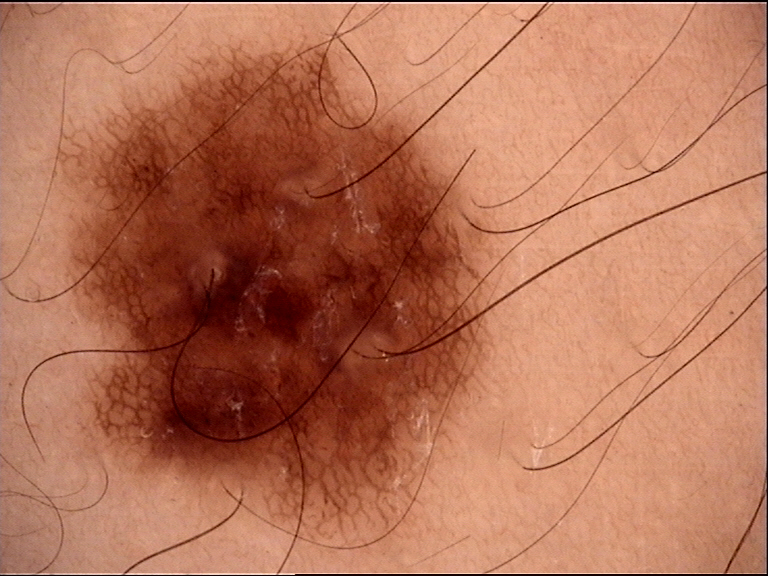<dermoscopy>
<image>dermoscopy</image>
<diagnosis>
<name>dysplastic junctional nevus</name>
<code>jd</code>
<malignancy>benign</malignancy>
<super_class>melanocytic</super_class>
<confirmation>expert consensus</confirmation>
</diagnosis>
</dermoscopy>